A skin lesion imaged with a dermatoscope.
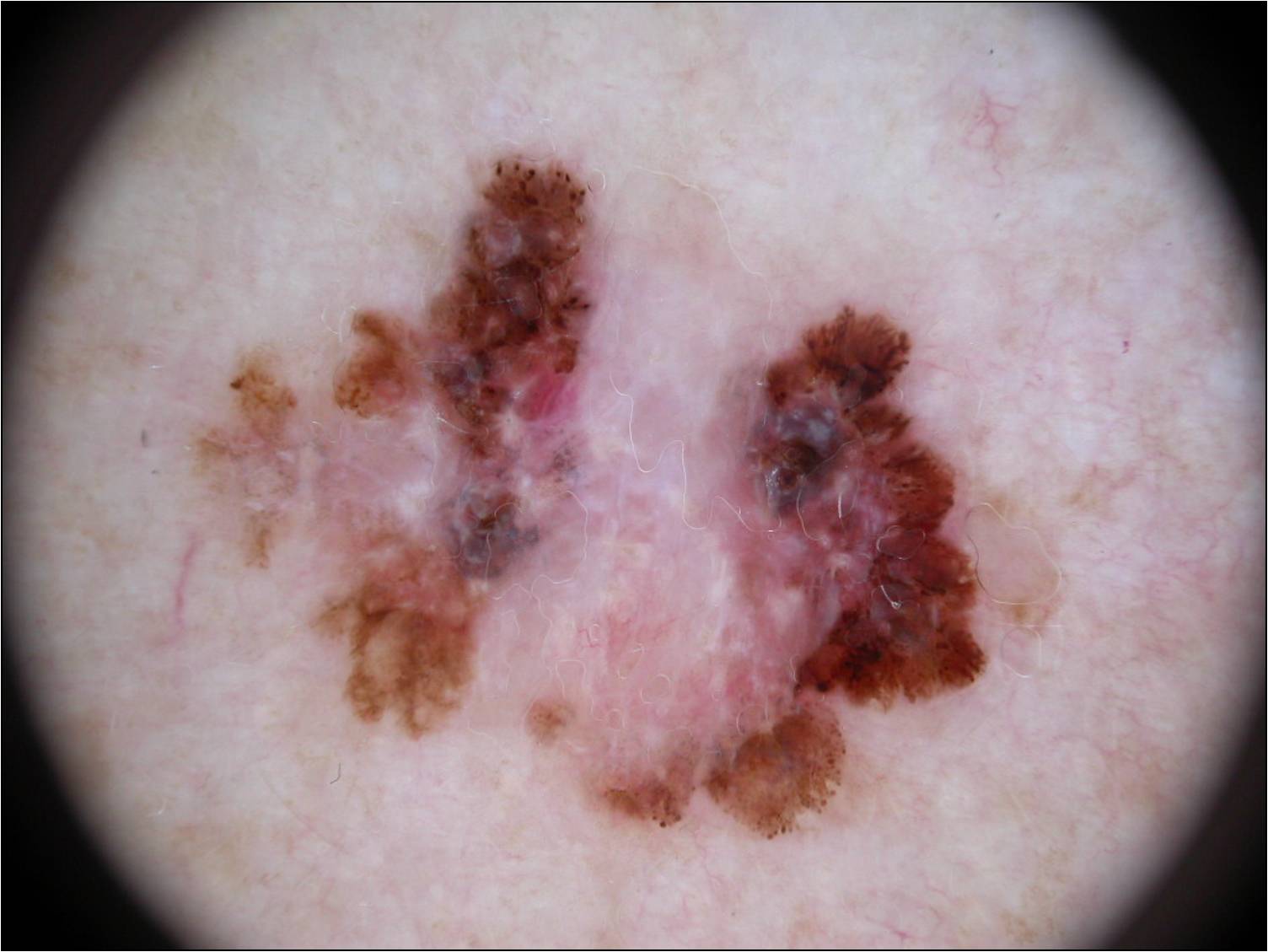Q: Where is the lesion located?
A: <box>158, 126, 1005, 847</box>
Q: What is the diagnosis?
A: a melanoma, a malignant skin lesion